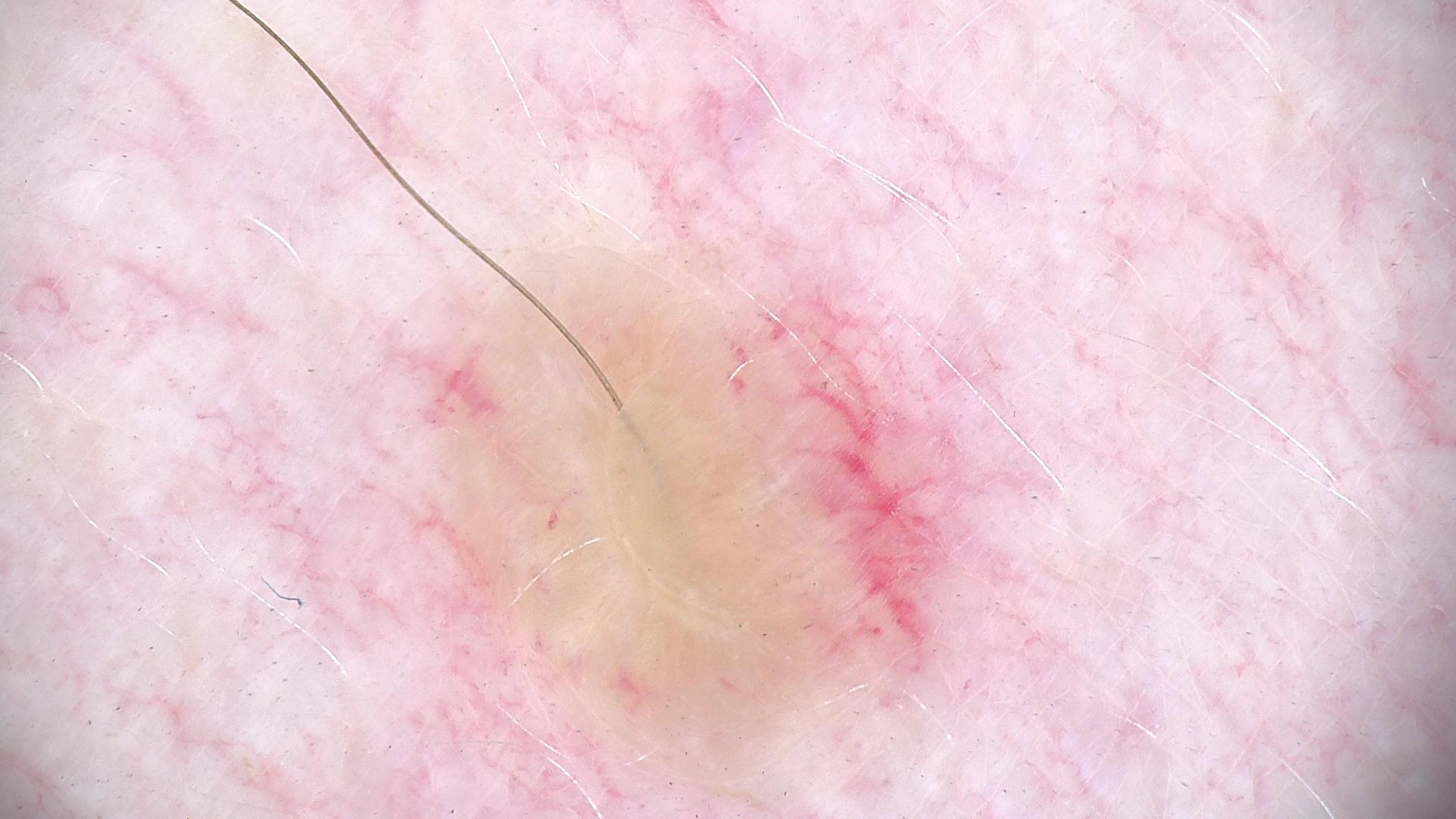Summary:
The morphology is that of a banal lesion.
Conclusion:
The diagnosis was a dermal nevus.